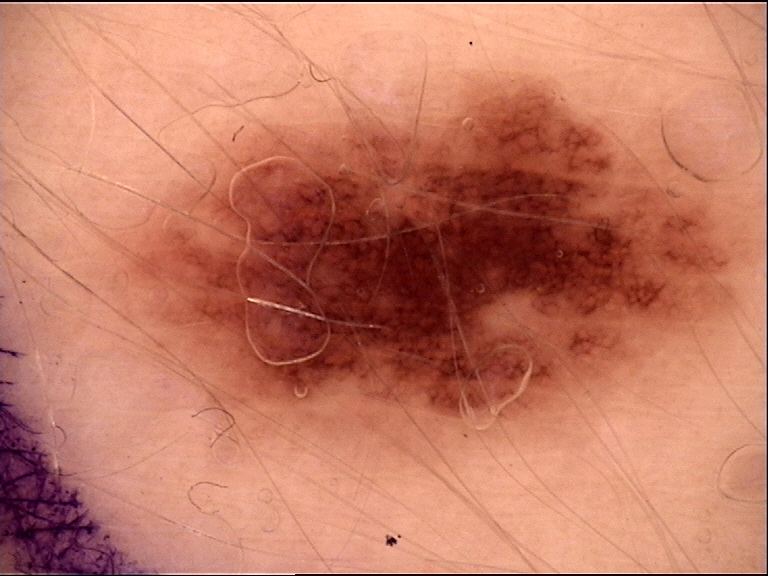The diagnosis was a dysplastic junctional nevus.